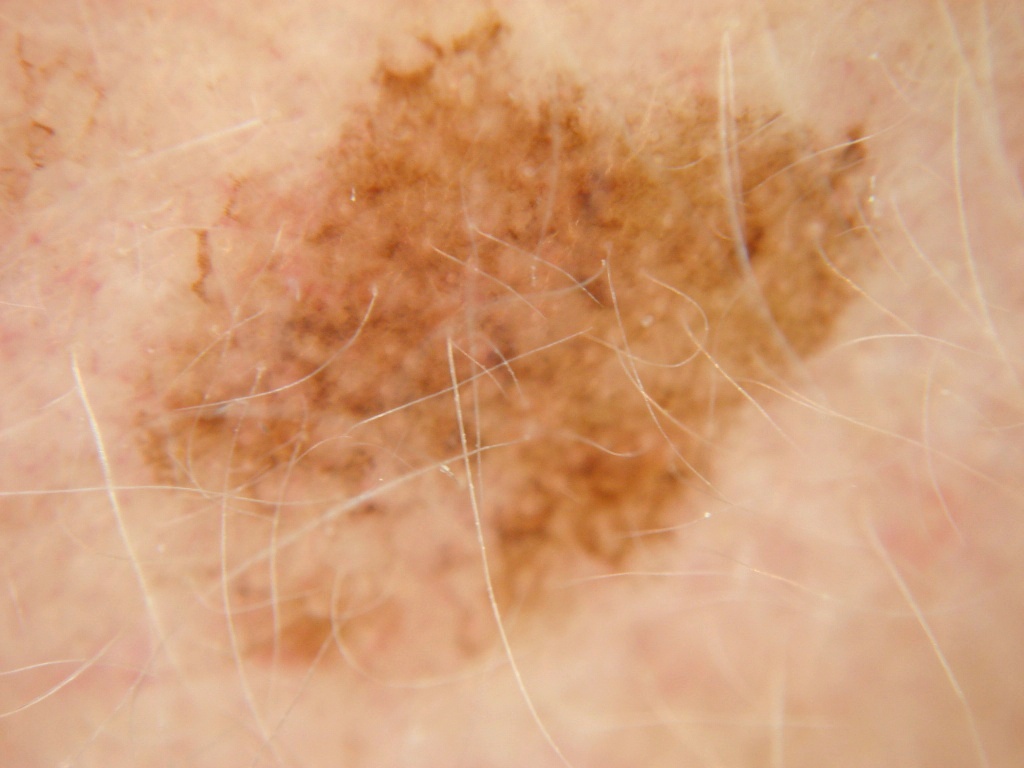Case summary:
A dermoscopic image of a skin lesion. As (left, top, right, bottom), the lesion is bounded by bbox(115, 3, 888, 695).
Conclusion:
Biopsy-confirmed as a malignant skin lesion.